The patient considered this a rash. The affected area is the head or neck. Close-up view. The lesion is described as rough or flaky. Symptoms reported: darkening, enlargement, pain, bothersome appearance, burning and itching. No constitutional symptoms were reported. Present for since childhood.
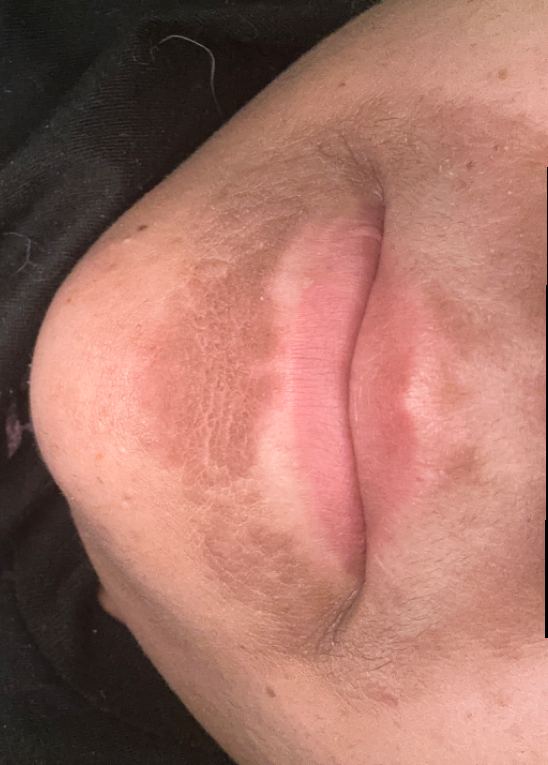Assessment:
On teledermatology review, Acanthosis nigricans (favored); Hyperkeratosis (possible); Irritant Contact Dermatitis (possible).